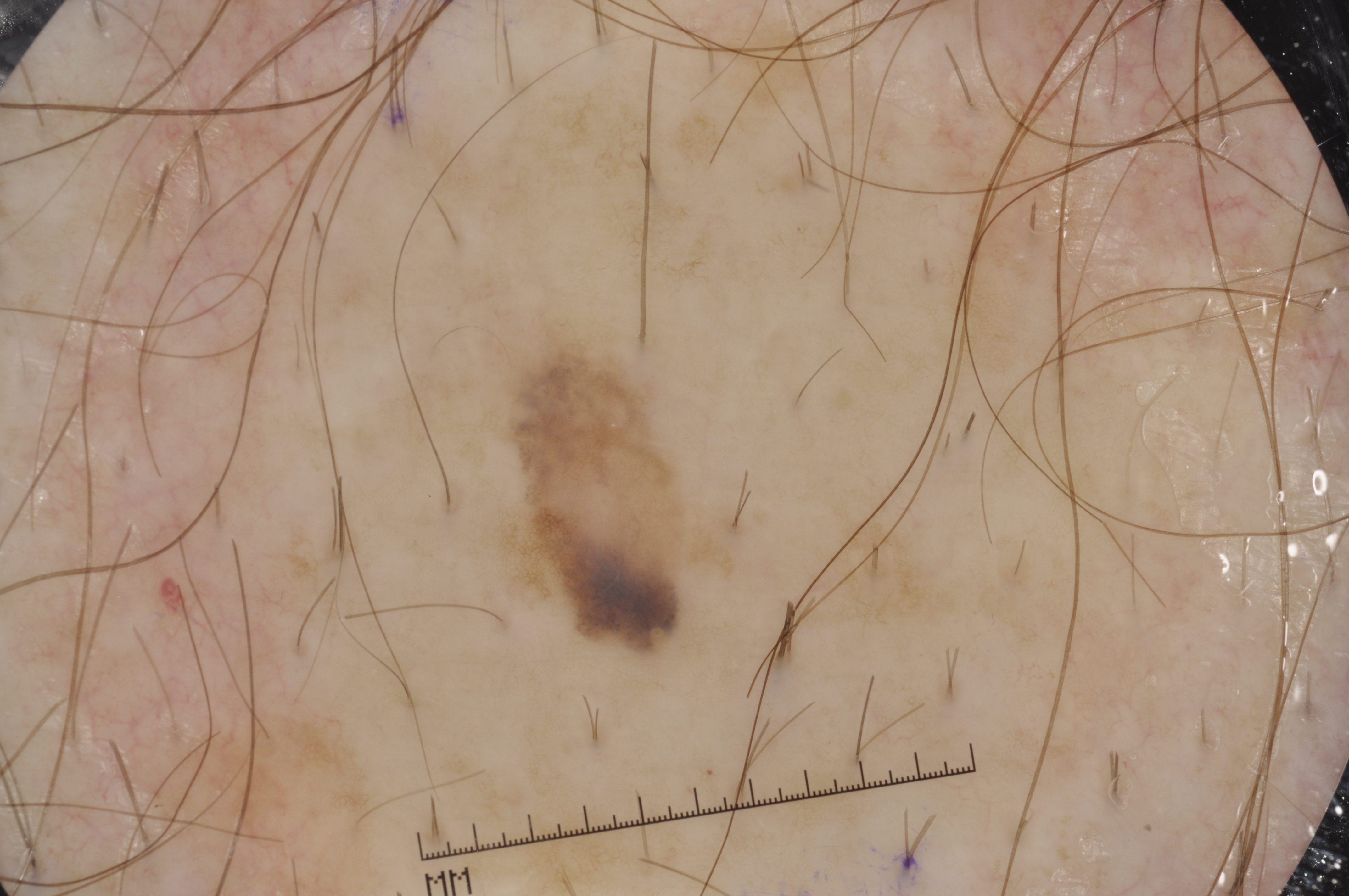Q: How was this image acquired?
A: dermoscopy
Q: What dermoscopic features are present?
A: milia-like cysts and pigment network; absent: negative network and streaks
Q: What is the lesion's bounding box?
A: (499, 337, 687, 660)
Q: What is this lesion?
A: a melanocytic nevus, a benign skin lesion